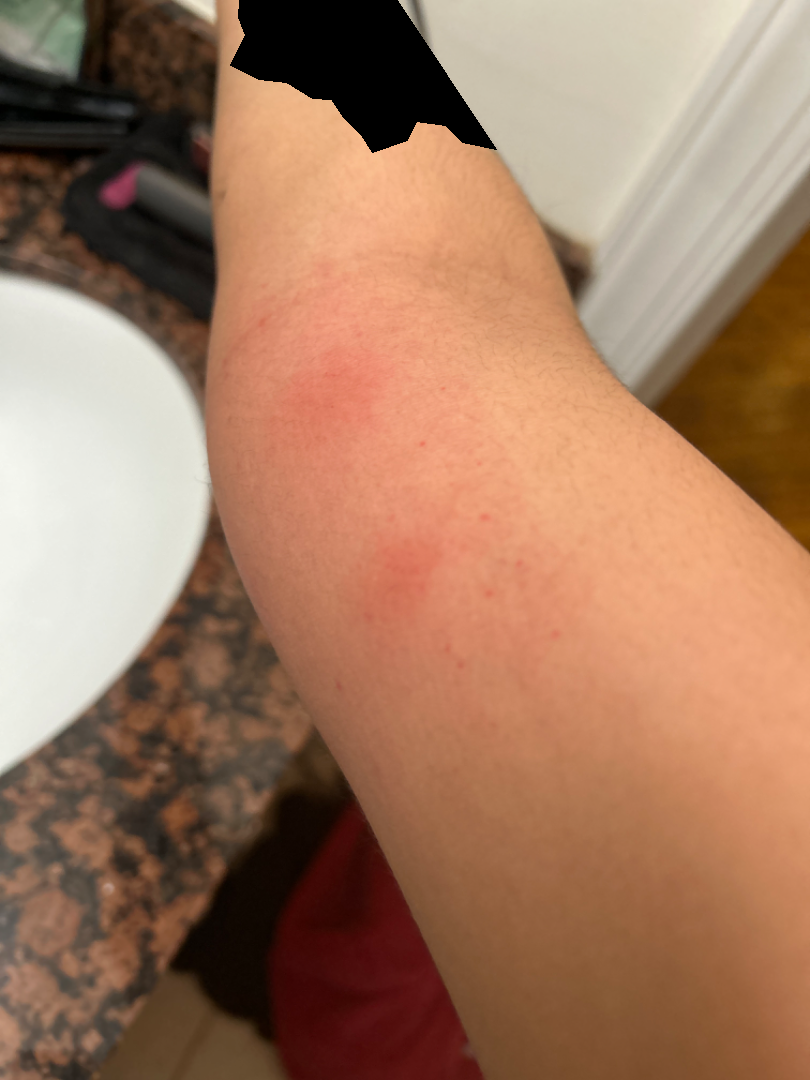Q: How does the patient describe it?
A: a rash
Q: What is the lesion texture?
A: raised or bumpy
Q: Where on the body?
A: arm
Q: Reported symptoms?
A: enlargement and itching
Q: When did this start?
A: about one day
Q: What is the framing?
A: close-up
Q: What is the differential diagnosis?
A: most consistent with Insect Bite; also consider Deep fungal infection; lower on the differential is panniculitis of skin